Close-up view; the affected area is the front of the torso and back of the torso; the patient is female.
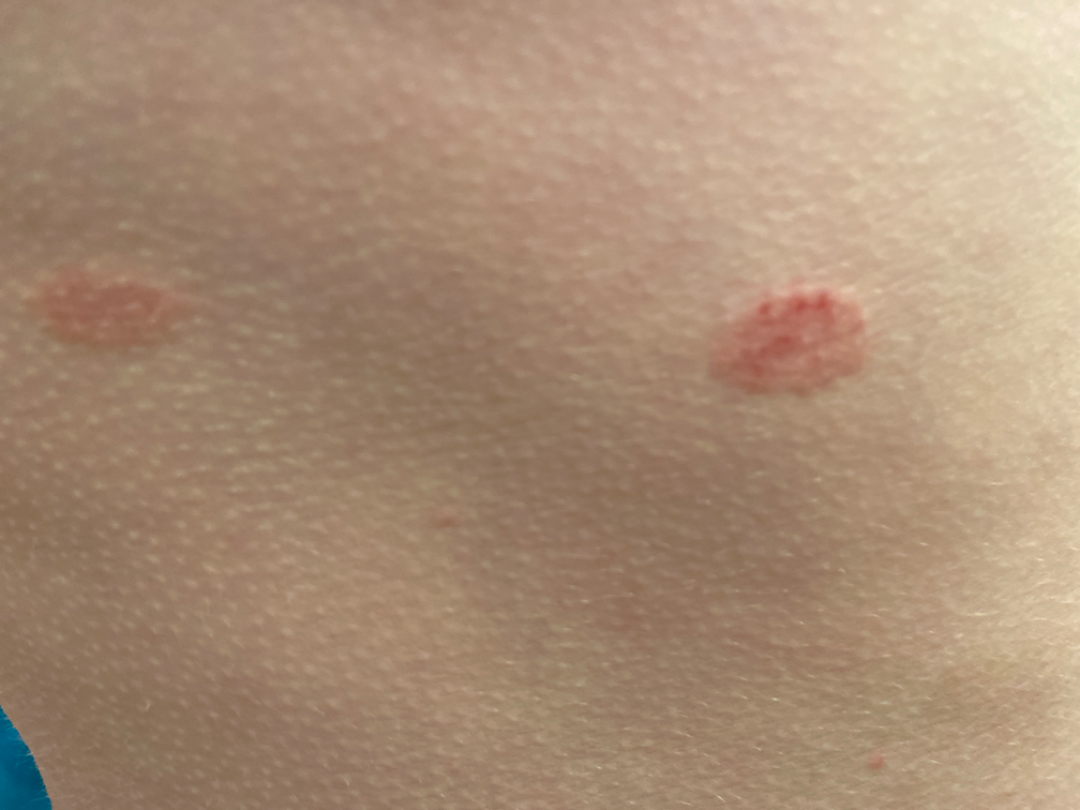On photographic review, Pityriasis rosea (favored); Psoriasis (considered); Eczema (lower probability).